A male subject aged 56. A clinical photo of a skin lesion taken with a smartphone — 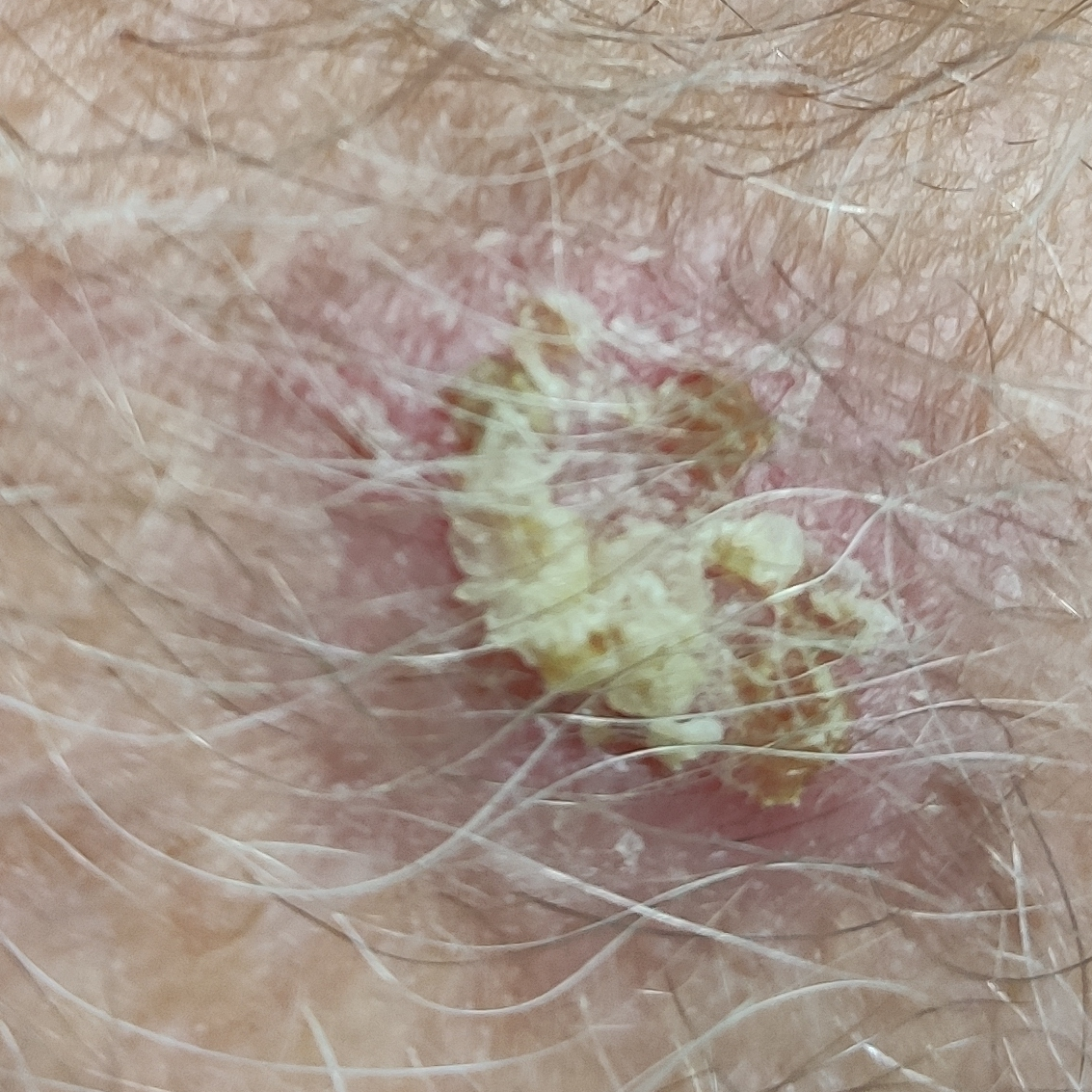The lesion is on a forearm.
Histopathologically confirmed as a basal cell carcinoma.